Dermoscopy of a skin lesion · a female patient roughly 45 years of age.
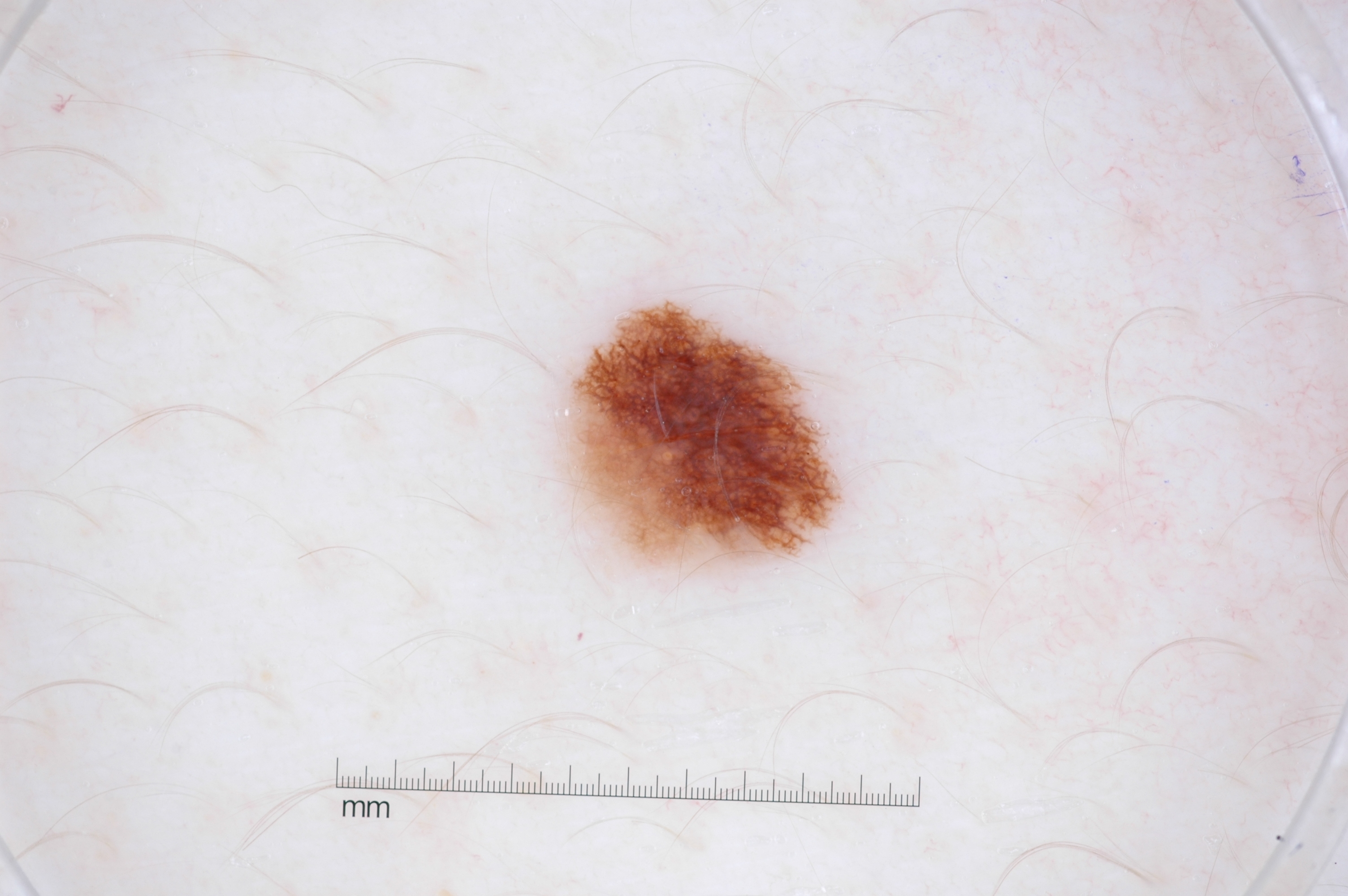Dermoscopically, the lesion shows pigment network, with no streaks, milia-like cysts, or negative network. The visible lesion spans (569, 308, 832, 567). A small lesion within a wider field of skin. The lesion was assessed as a melanocytic nevus, a benign skin lesion.